A dermoscopic photograph of a skin lesion:
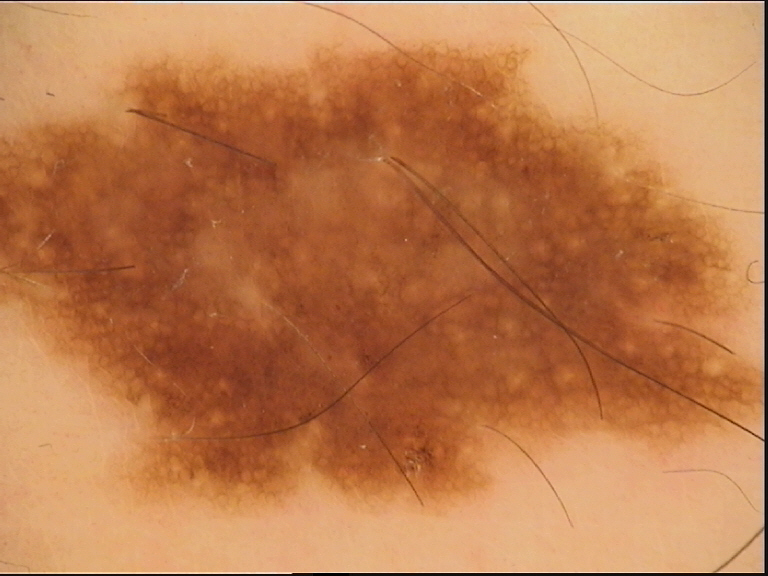diagnosis: dysplastic compound nevus (expert consensus).